A dermoscopy image of a single skin lesion.
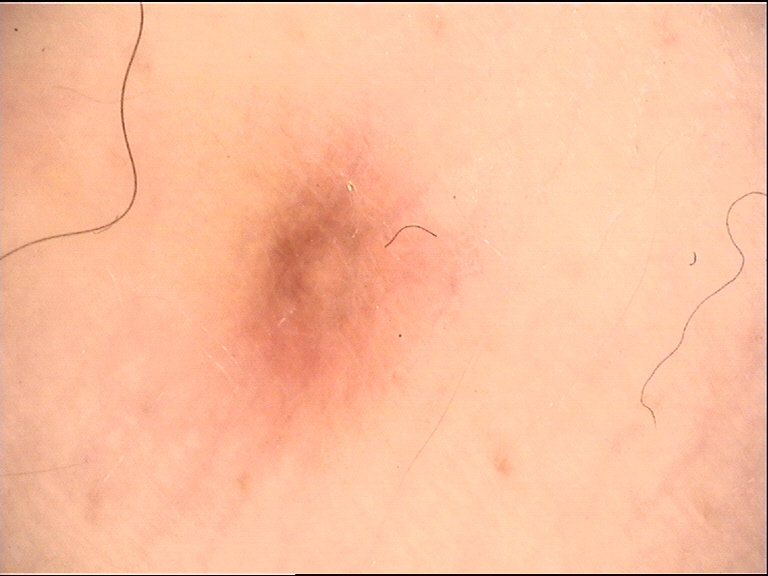Summary: The morphology is that of a fibro-histiocytic lesion. Conclusion: Classified as a benign lesion — a dermatofibroma.